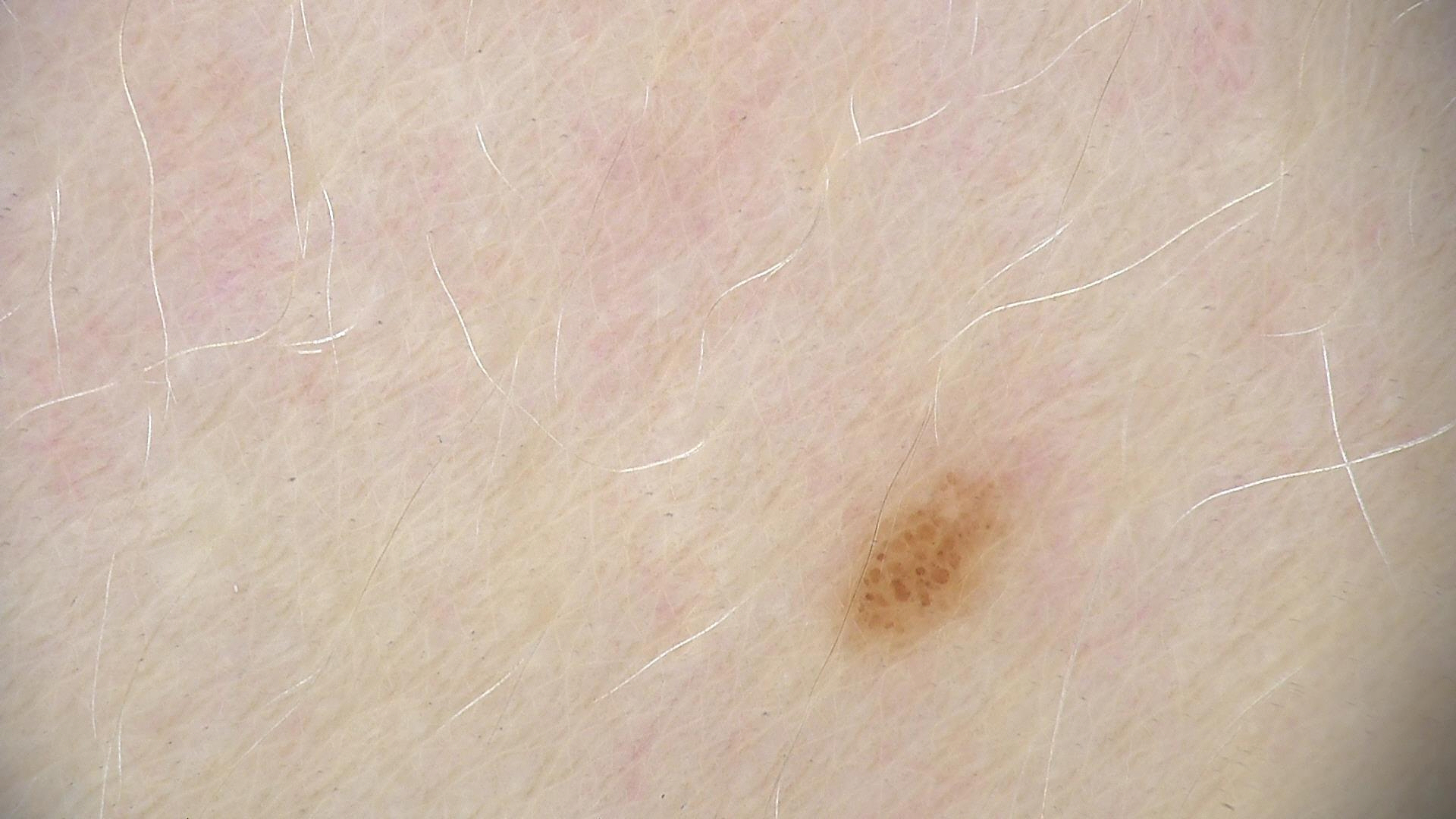{"diagnosis": {"name": "dysplastic junctional nevus", "code": "jd", "malignancy": "benign", "super_class": "melanocytic", "confirmation": "expert consensus"}}